A dermoscopic photograph of a skin lesion.
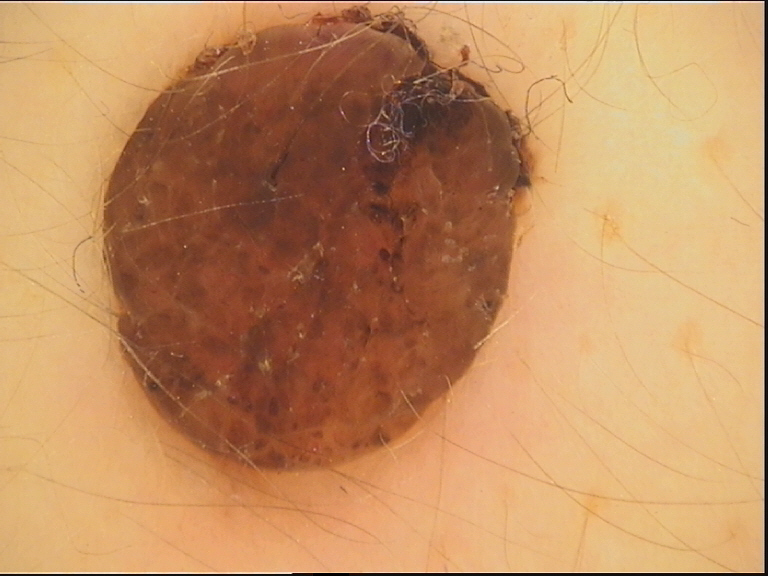subtype: banal | class: dermal nevus (expert consensus).